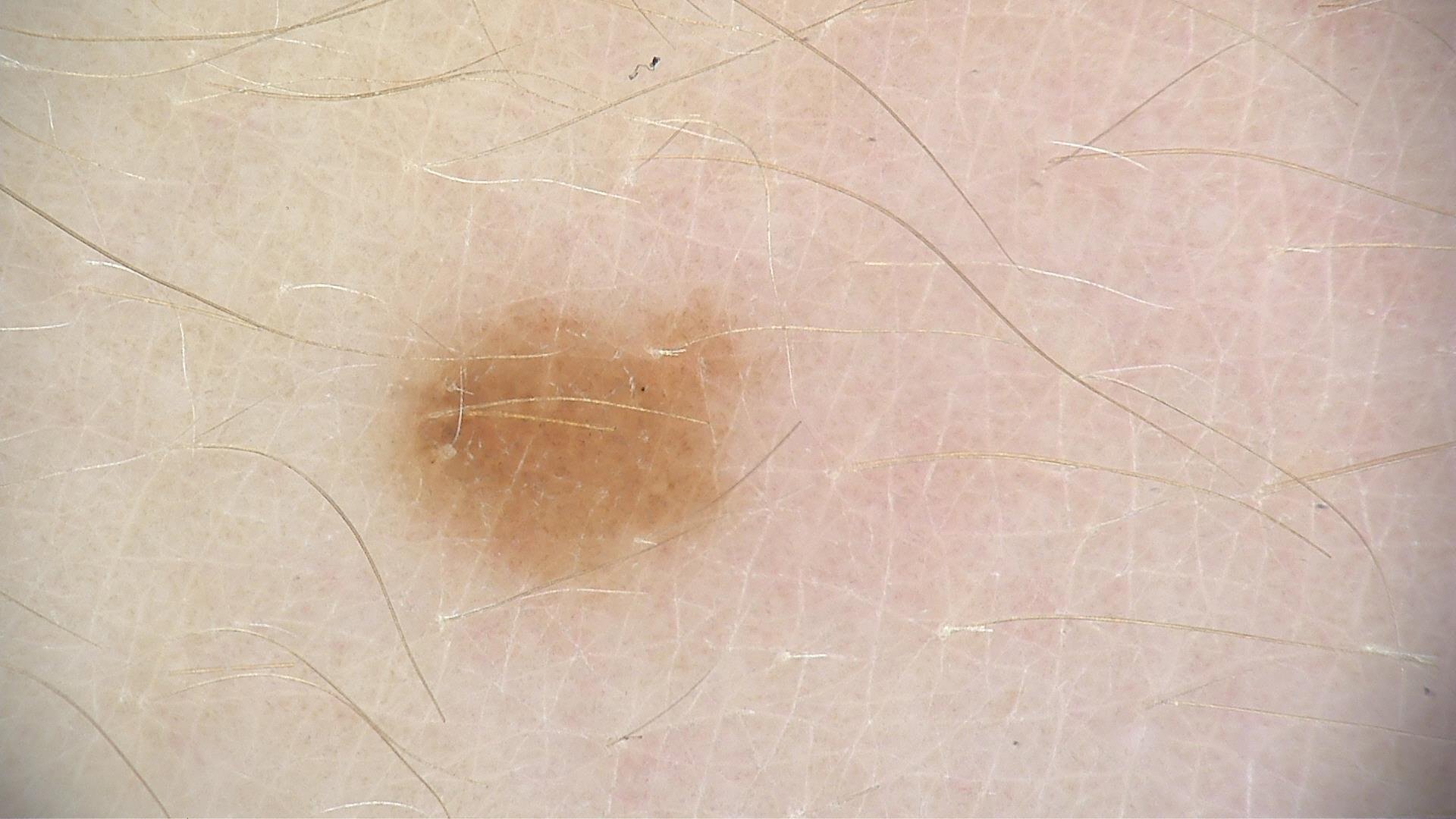Q: What is this lesion?
A: compound nevus (expert consensus)